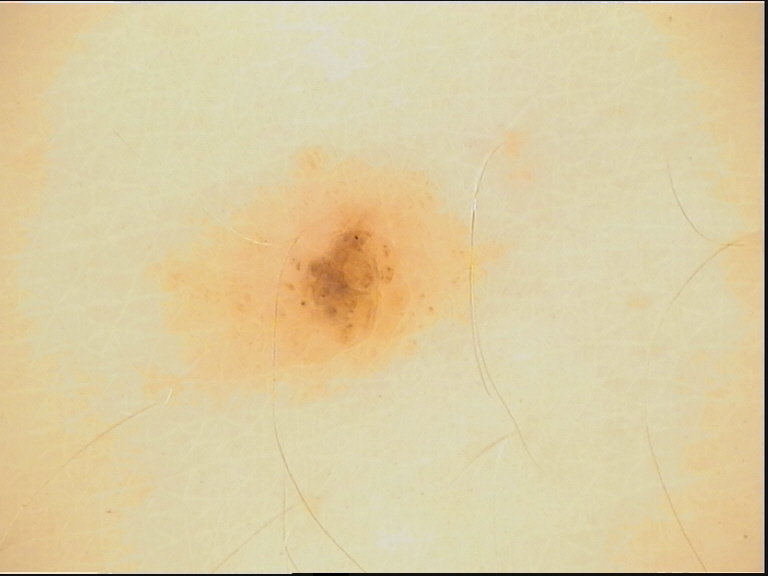The diagnostic label was a dysplastic compound nevus.